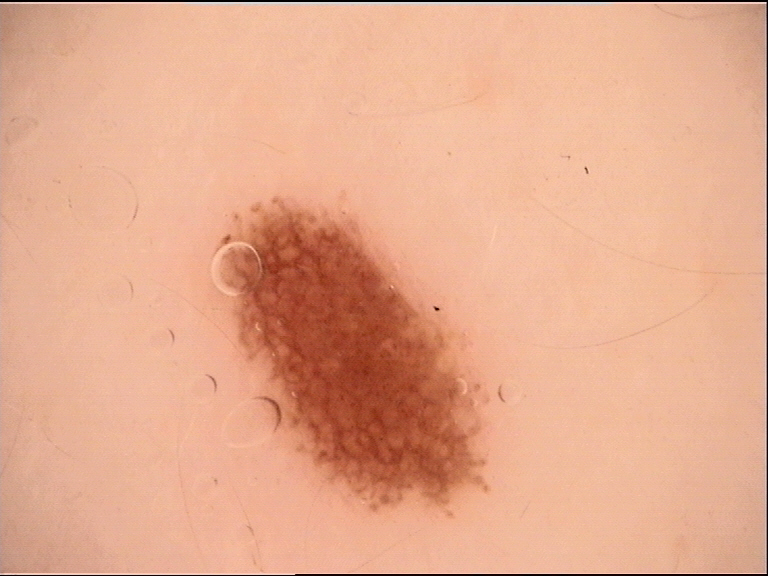<lesion>
<image>dermoscopy</image>
<diagnosis>
<name>dysplastic junctional nevus</name>
<code>jd</code>
<malignancy>benign</malignancy>
<super_class>melanocytic</super_class>
<confirmation>expert consensus</confirmation>
</diagnosis>
</lesion>